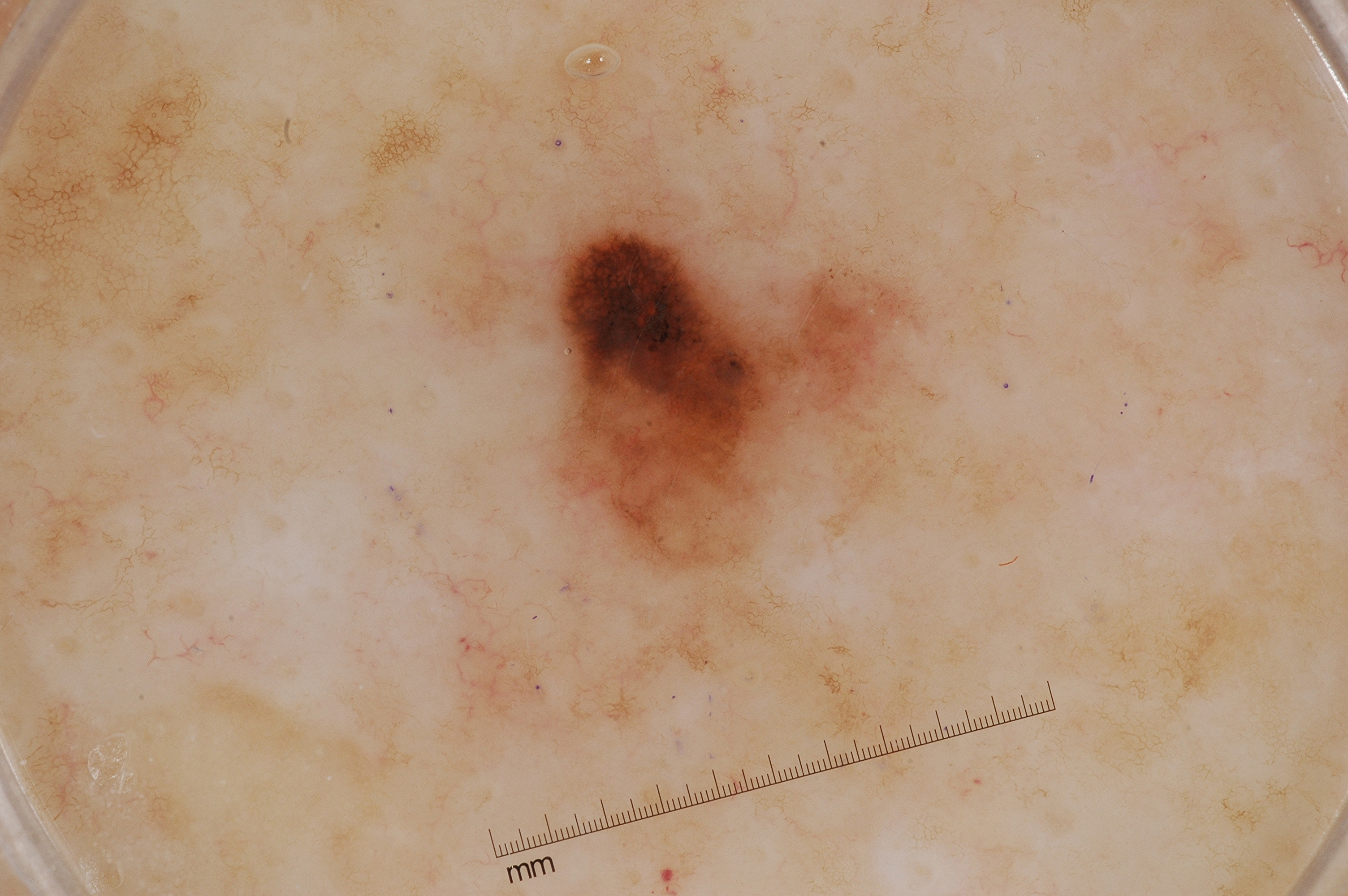patient: female, aged approximately 70 | image: dermoscopy | lesion location: [548,196,916,574] | extent: ~8% of the field | dermoscopic findings: milia-like cysts and pigment network | diagnosis: a melanoma.